A dermoscopic image of a skin lesion: 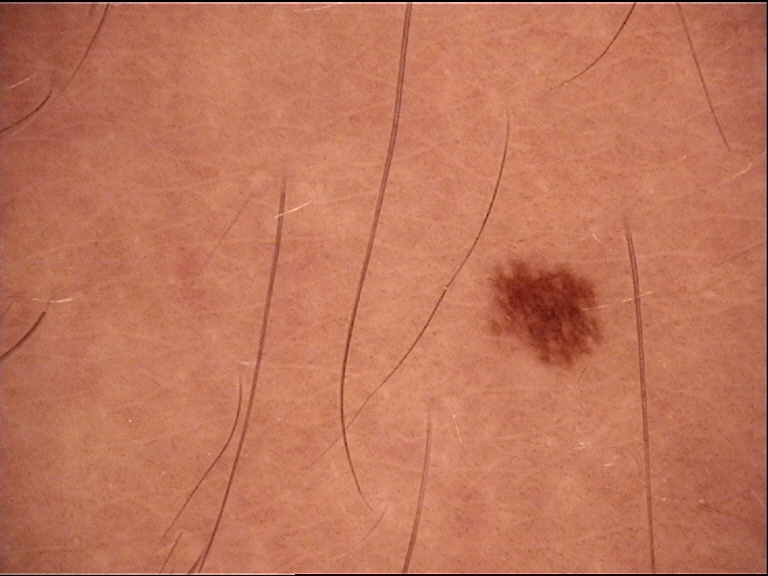subtype — banal | label — junctional nevus (expert consensus).